A skin lesion imaged with a dermatoscope.
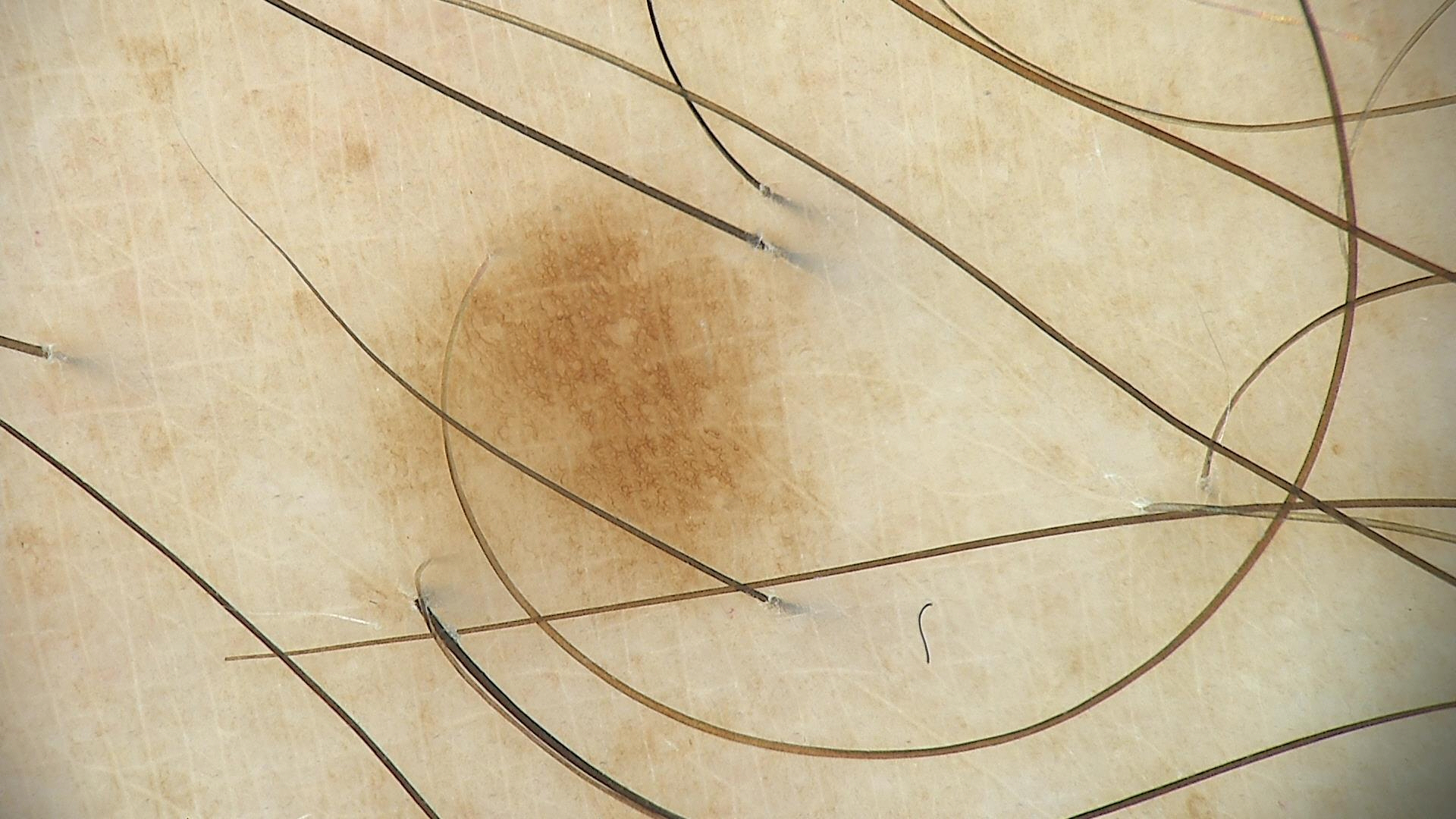assessment = lentigo simplex (expert consensus).